A clinical photograph of a skin lesion; a patient aged 69:
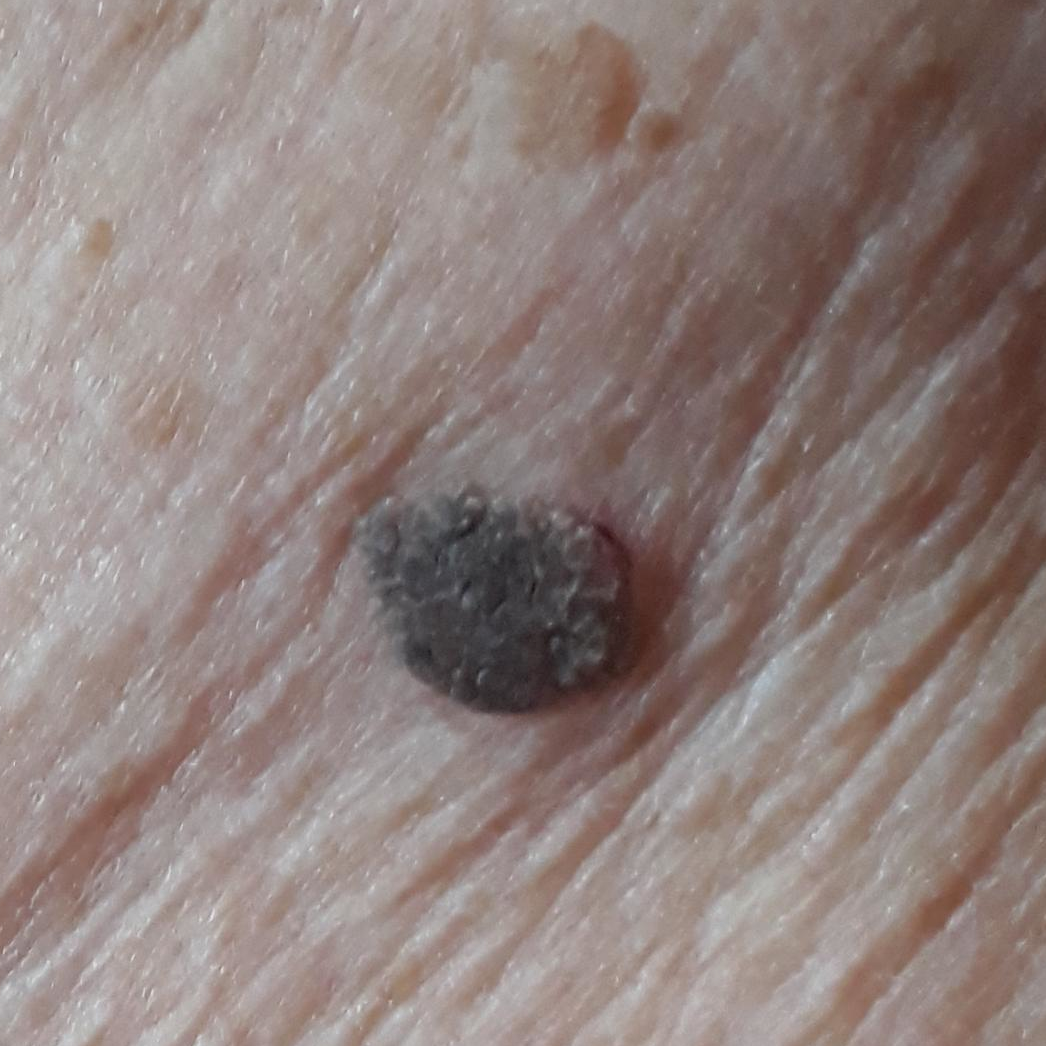site=the chest; impression=seborrheic keratosis (clinical consensus).